Self-categorized by the patient as a rash. The front of the torso is involved. The patient is a female aged 40–49. Texture is reported as raised or bumpy. The photograph was taken at a distance: 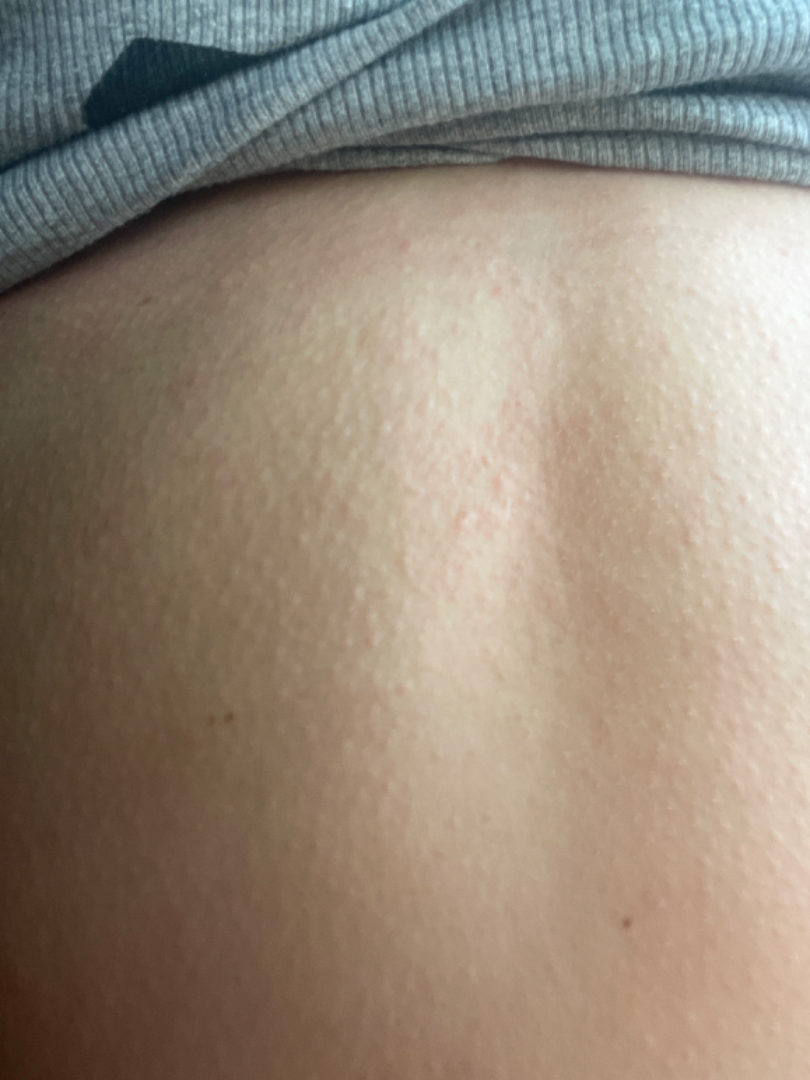One reviewing dermatologist: Tinea Versicolor, Psoriasis and Eczema were considered with similar weight.